The patient considered this a rash. Symptoms reported: burning, bothersome appearance, itching and enlargement. The patient indicates the lesion is rough or flaky. This is a close-up image. The lesion involves the head or neck. Non-clinician graders estimated MST 3–4. The patient reported no systemic symptoms. Reported duration is less than one week.
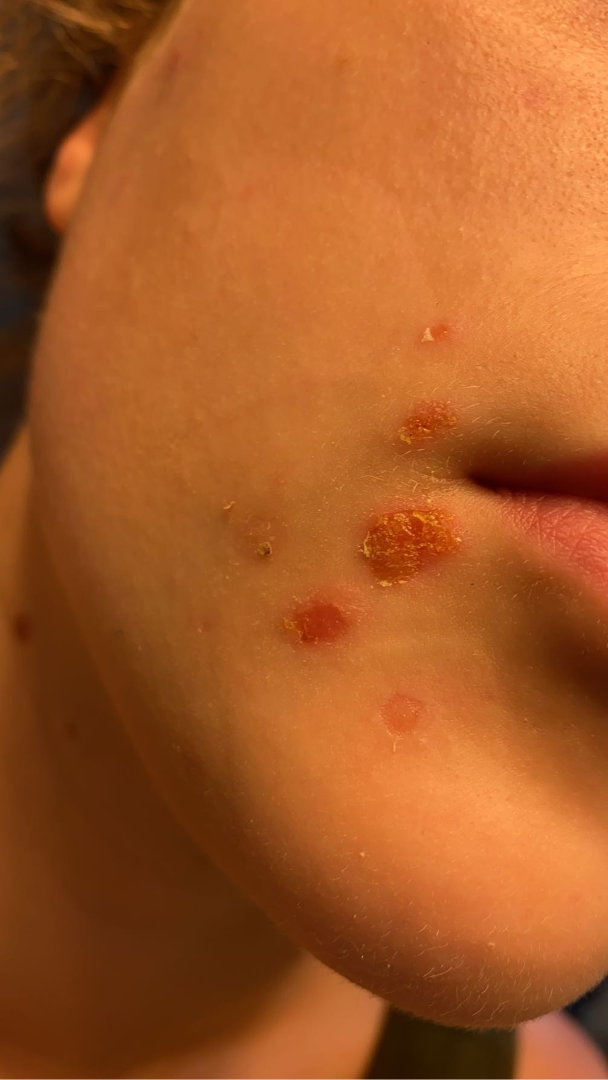Notes:
– dermatologist impression — one reviewing dermatologist: the leading consideration is Impetigo; possibly Eczema; an alternative is Allergic Contact Dermatitis